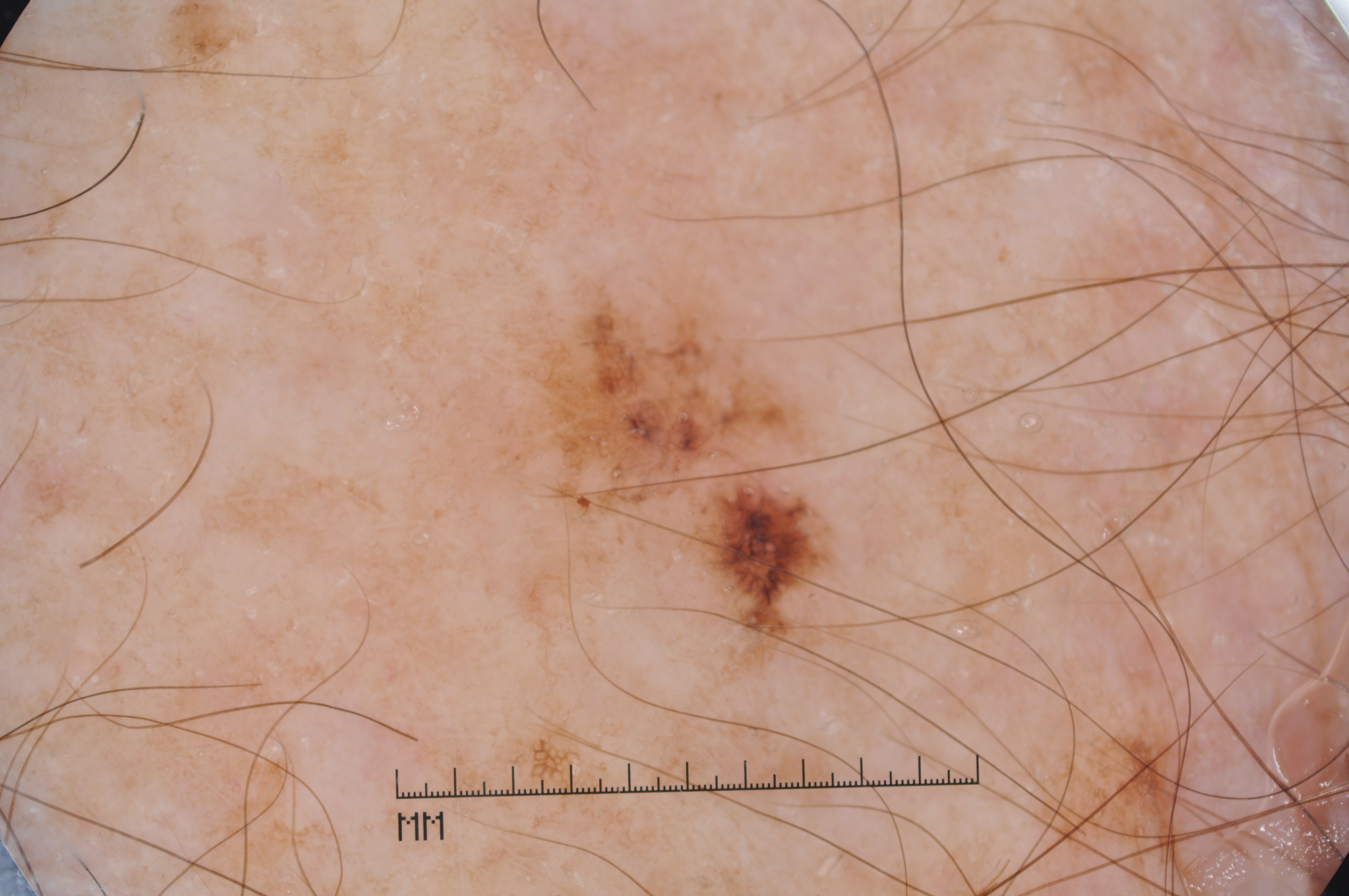| feature | finding |
|---|---|
| subject | male, aged approximately 80 |
| image type | dermoscopy of a skin lesion |
| dermoscopic findings | pigment network; absent: negative network, streaks, and milia-like cysts |
| lesion bbox | [538, 309, 811, 567] |
| diagnostic label | a melanoma |